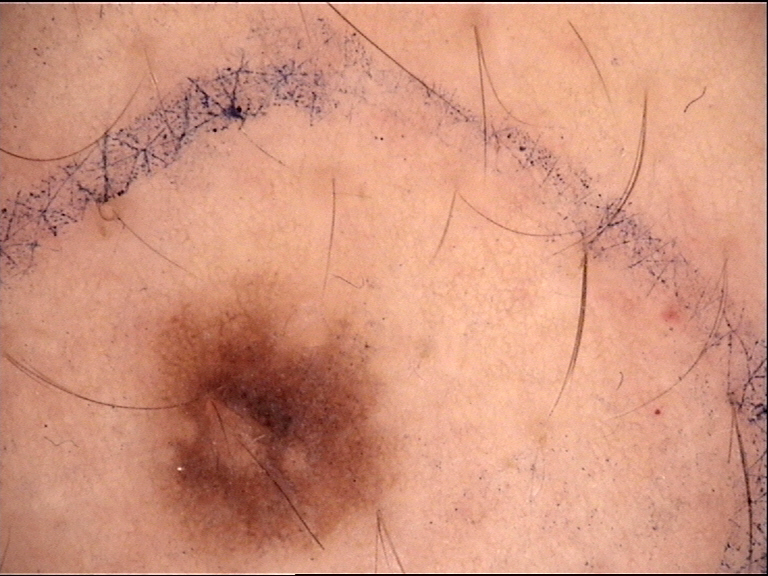The diagnosis was a dysplastic junctional nevus.